A female subject 81 years of age. The patient says their skin reddens painfully with sun exposure. A moderate number of moles by the patient's own estimate. A clinical photograph of a skin lesion. Collected as part of a research study, without a referral diagnosis: 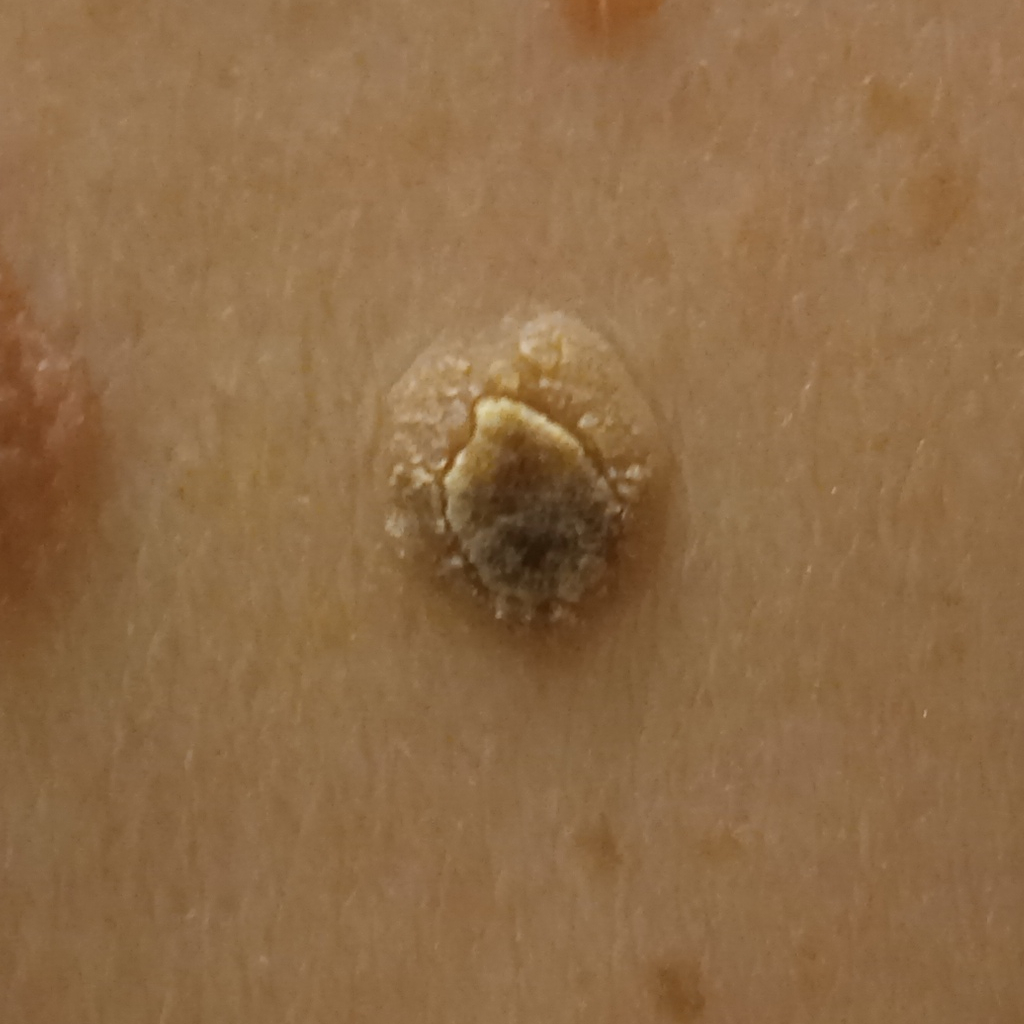Case summary: Located on the back. The lesion measures approximately 9.8 mm. Impression: The dermatologists' assessment was a seborrheic keratosis.